Located on the arm · the patient considered this a rash · an image taken at an angle · the patient indicates itching, enlargement and bothersome appearance: 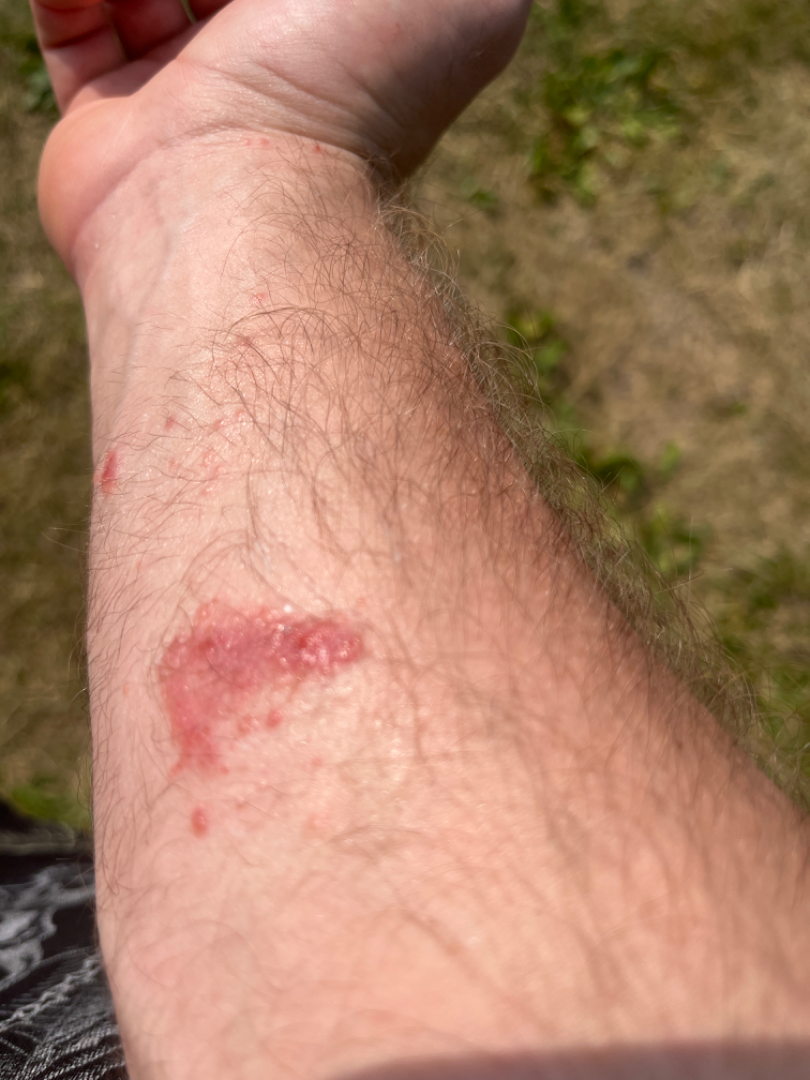The dermatologist could not determine a likely condition from the photograph alone.